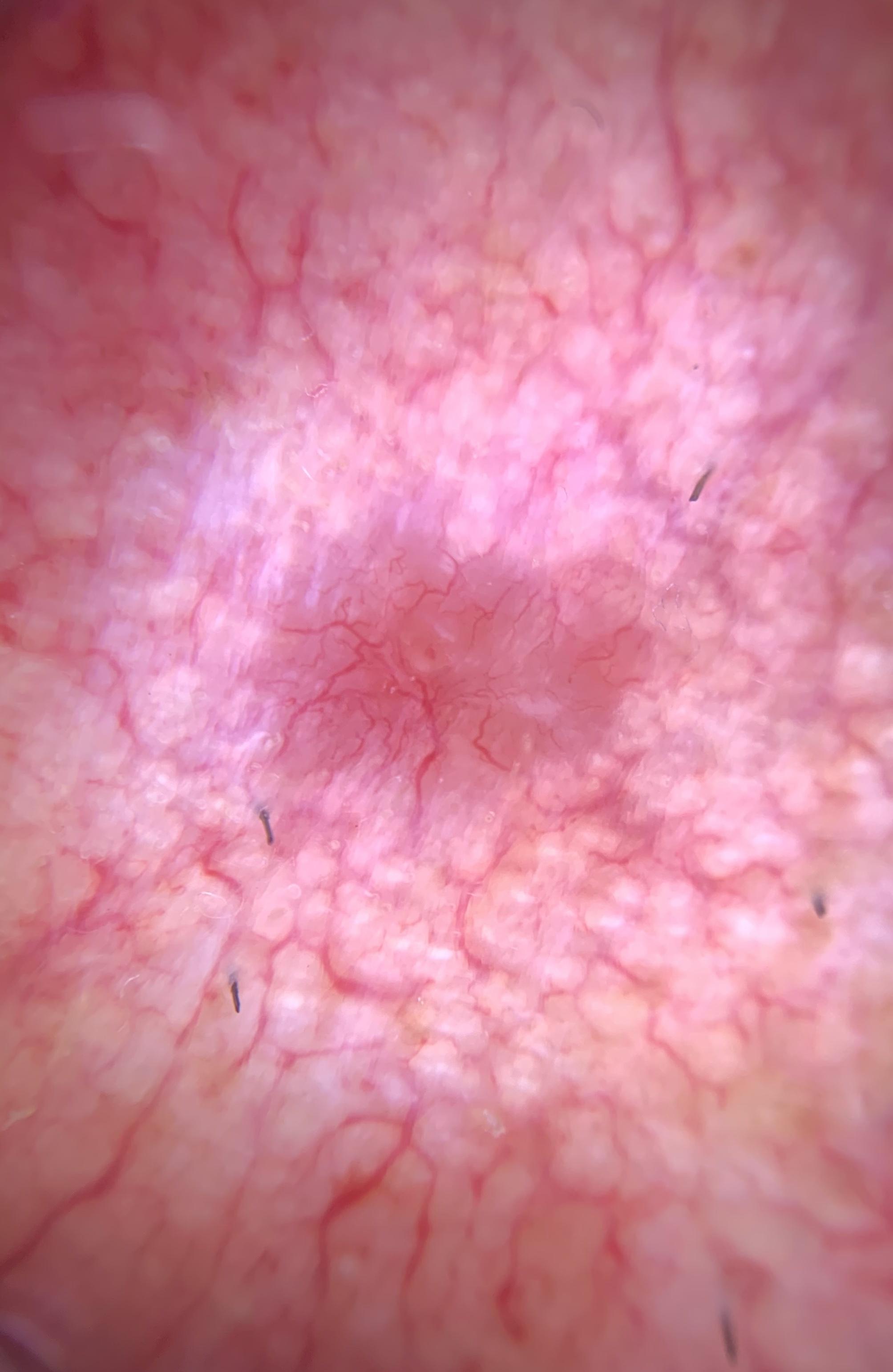{"patient": {"age_approx": 70, "sex": "male"}, "skin_type": "II", "image": "dermoscopic image", "lesion_location": {"region": "the head or neck"}, "diagnosis": {"name": "Basal cell carcinoma", "malignancy": "malignant", "confirmation": "histopathology", "lineage": "adnexal"}}